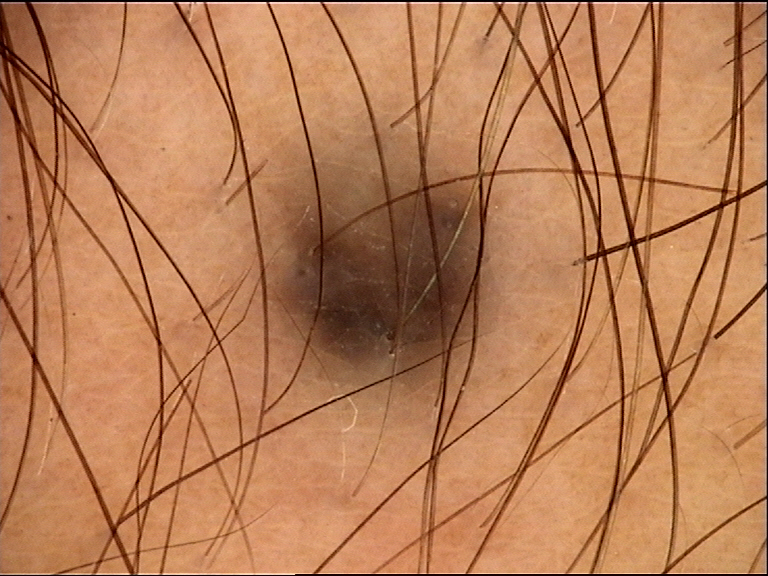imaging — dermatoscopy; diagnosis — blue nevus (expert consensus).